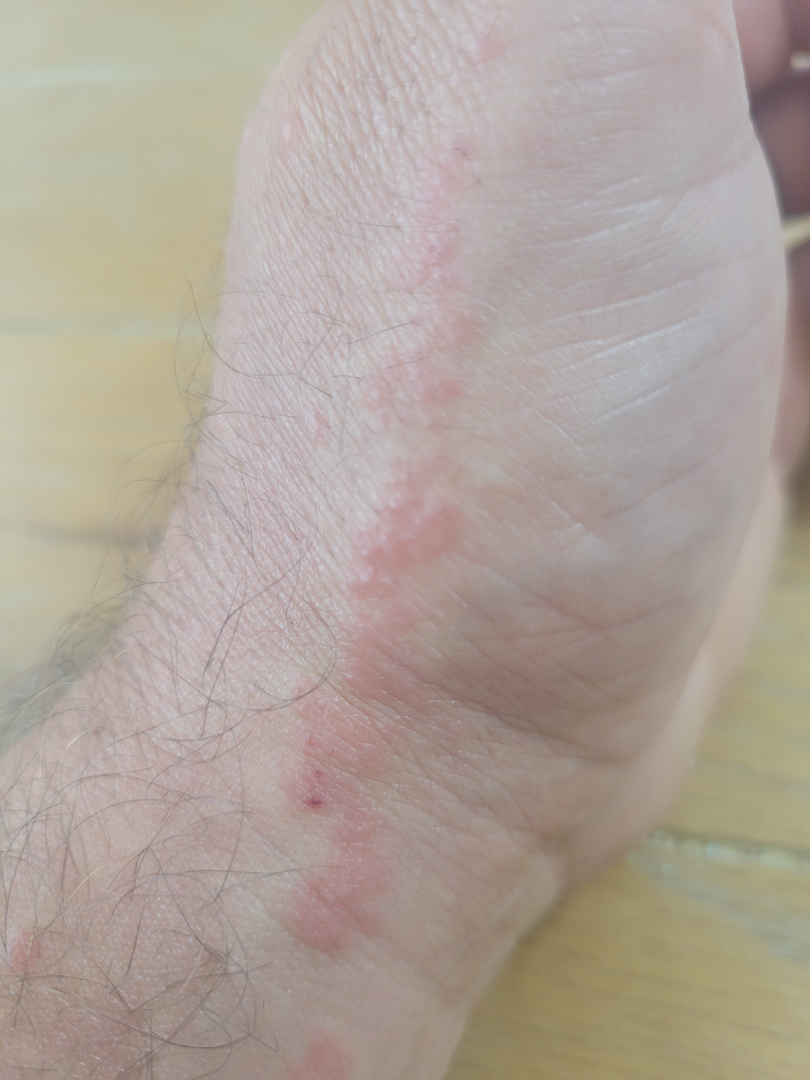assessment = ungradable on photographic review | location = back of the hand and arm | skin tone = Fitzpatrick phototype II; lay reviewers estimated Monk skin tone scale 1 or 2 | patient-reported symptoms = itching, bothersome appearance and enlargement | photo taken = close-up | lesion texture = raised or bumpy.